Acquired for a research image collection, with no referral diagnosis. A female patient age 15. The patient says their skin reddens with sun exposure. On a questionnaire the patient reported no prior organ transplant and no personal history of cancer. The patient describes having few moles overall. A clinical close-up of a skin lesion:
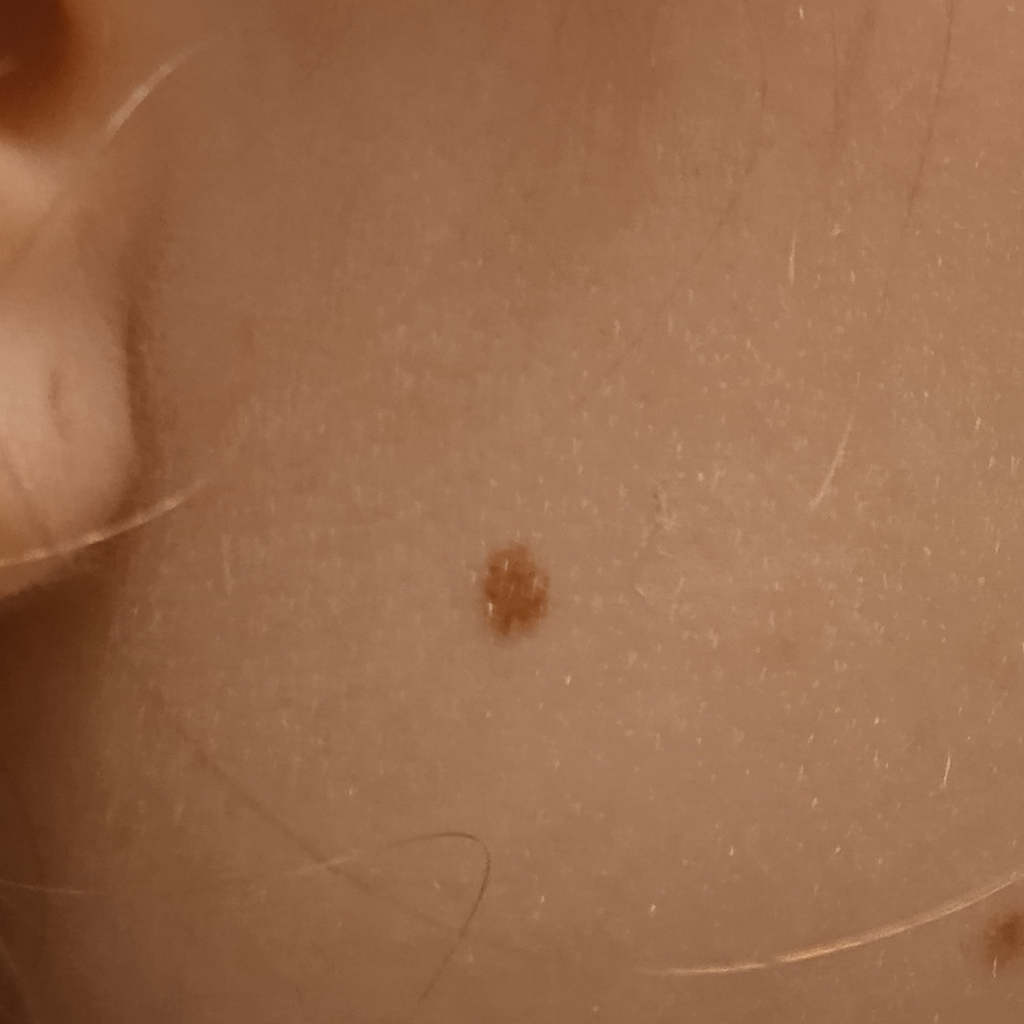{
  "lesion_location": "the face",
  "lesion_size": {
    "diameter_mm": 3.6
  },
  "diagnosis": {
    "name": "melanocytic nevus",
    "malignancy": "benign"
  }
}